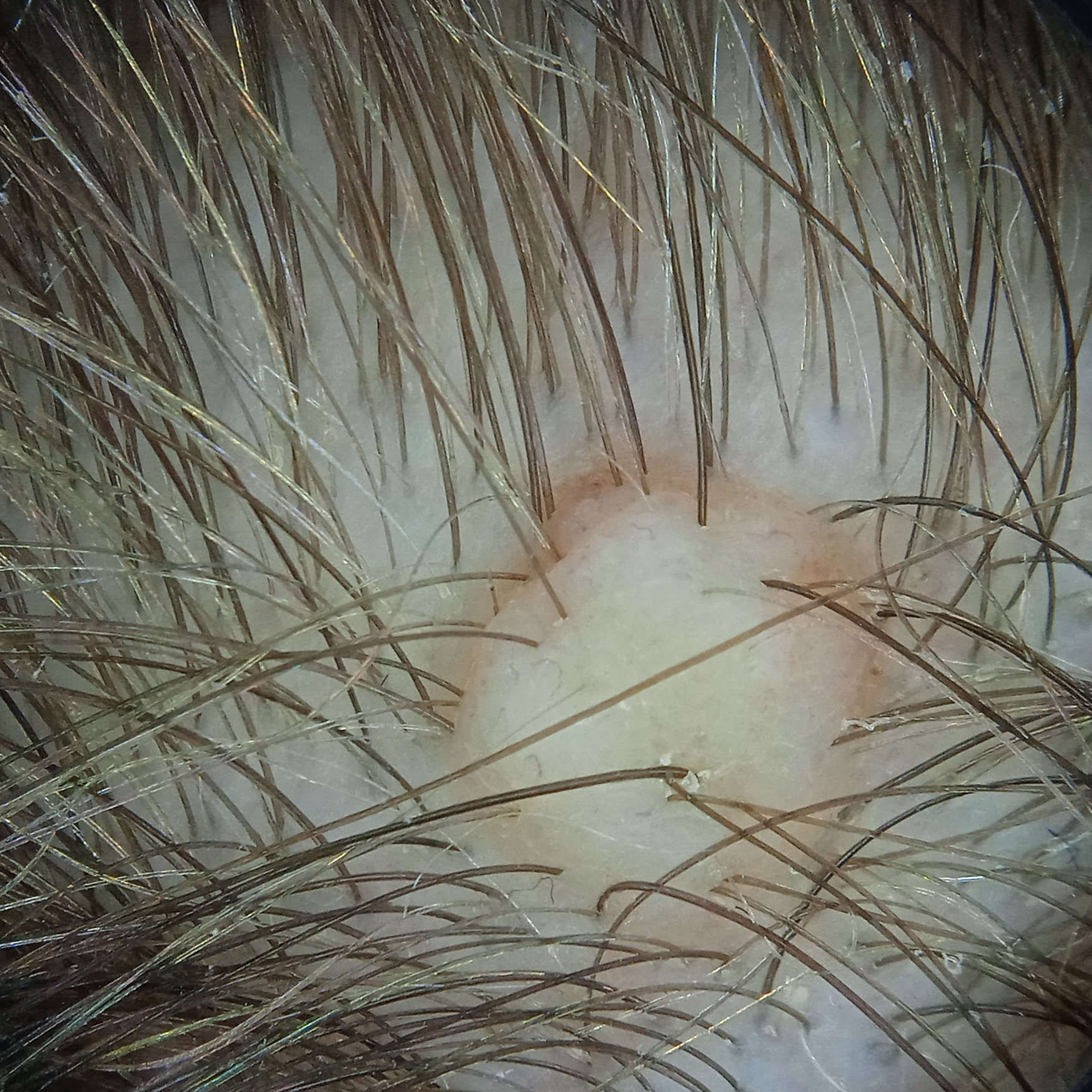modality — dermatoscopic image | subject — female, 15 years of age | sun reaction — skin reddens with sun exposure | location — the head | lesion size — 5 mm | diagnosis — melanocytic nevus (biopsy-proven).